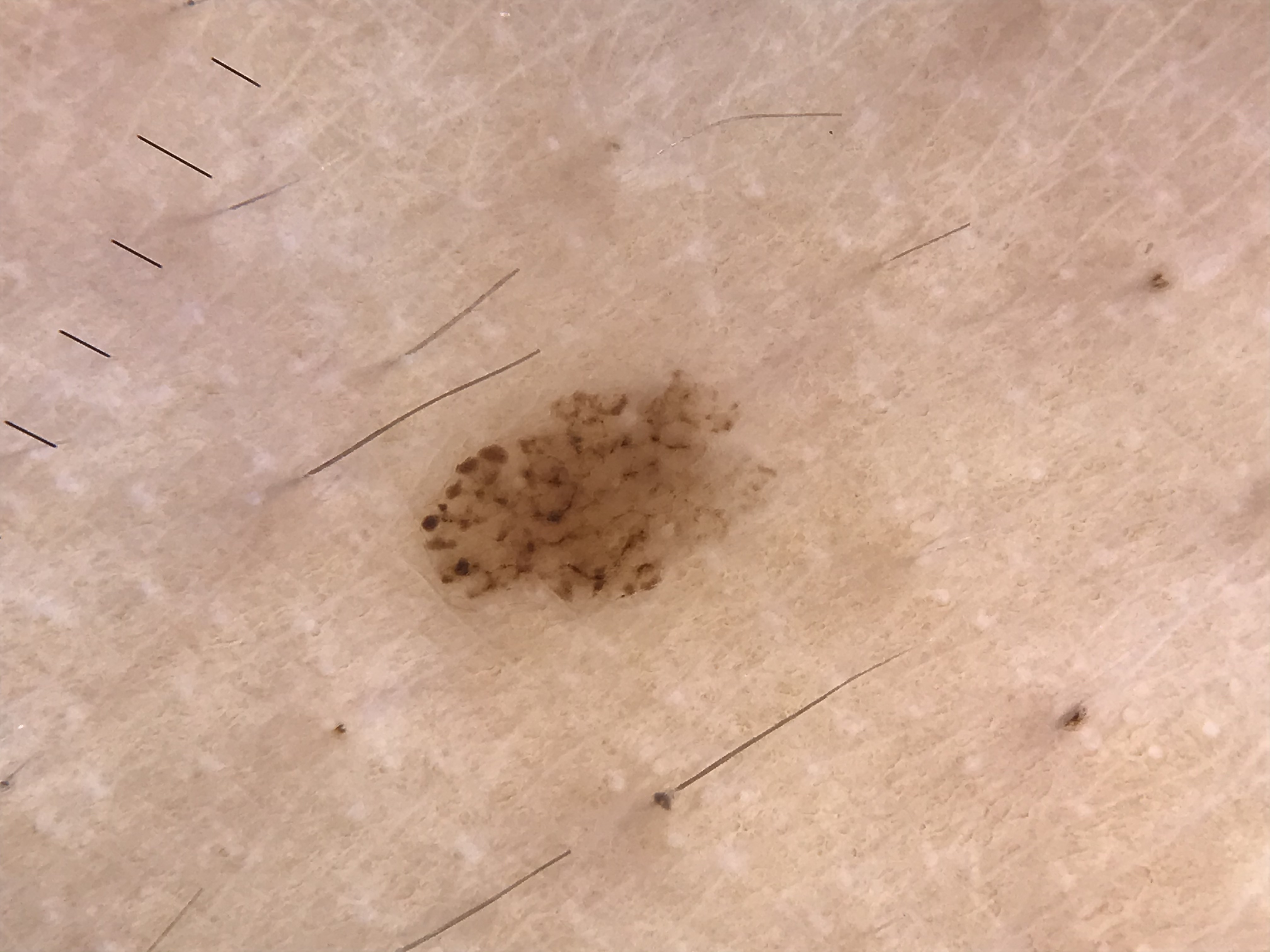{"diagnosis": {"name": "dysplastic compound nevus", "code": "cd", "malignancy": "benign", "super_class": "melanocytic", "confirmation": "expert consensus"}}